A female patient aged 27. Collected as part of a research study, without a referral diagnosis. A macroscopic clinical photograph of a skin lesion. The patient says their skin reddens with sun exposure: 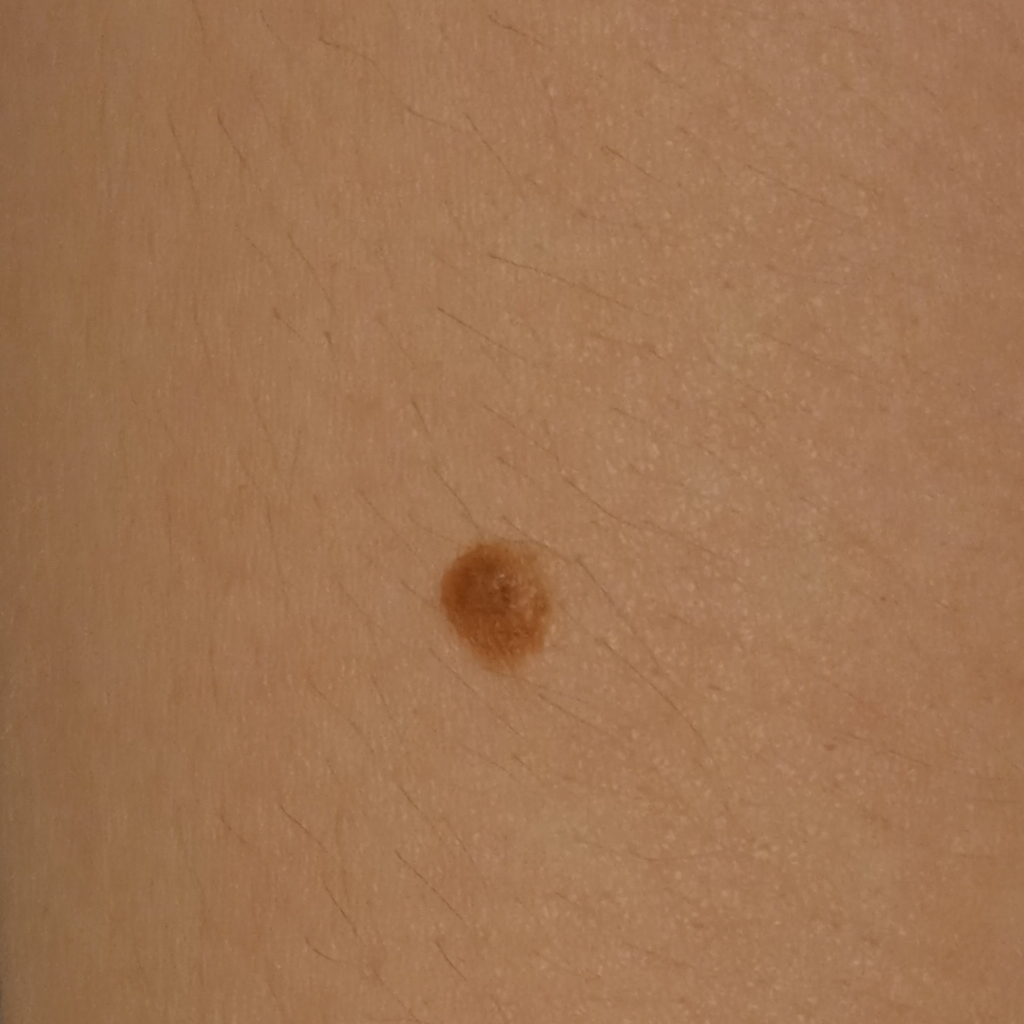Q: What is the anatomic site?
A: the torso
Q: What was the diagnosis?
A: melanocytic nevus (dermatologist consensus)